A dermoscopic close-up of a skin lesion — 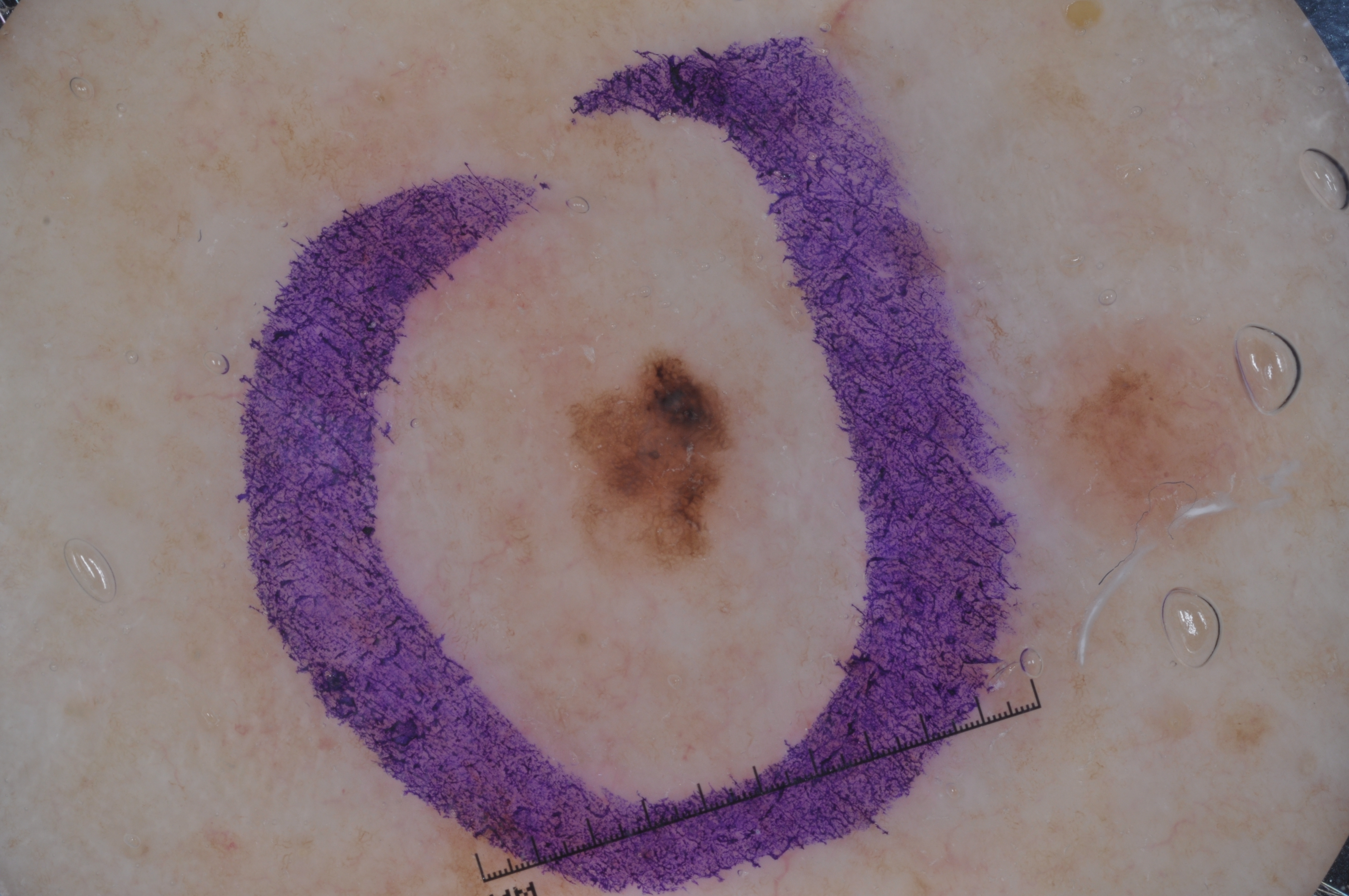location = 561/347/743/572; impression = a melanoma.